The condition has been present for one to four weeks; this is a close-up image; the patient reported no systemic symptoms; the leg is involved; the patient considered this a rash; texture is reported as raised or bumpy; reported lesion symptoms include enlargement, bothersome appearance, burning and itching:
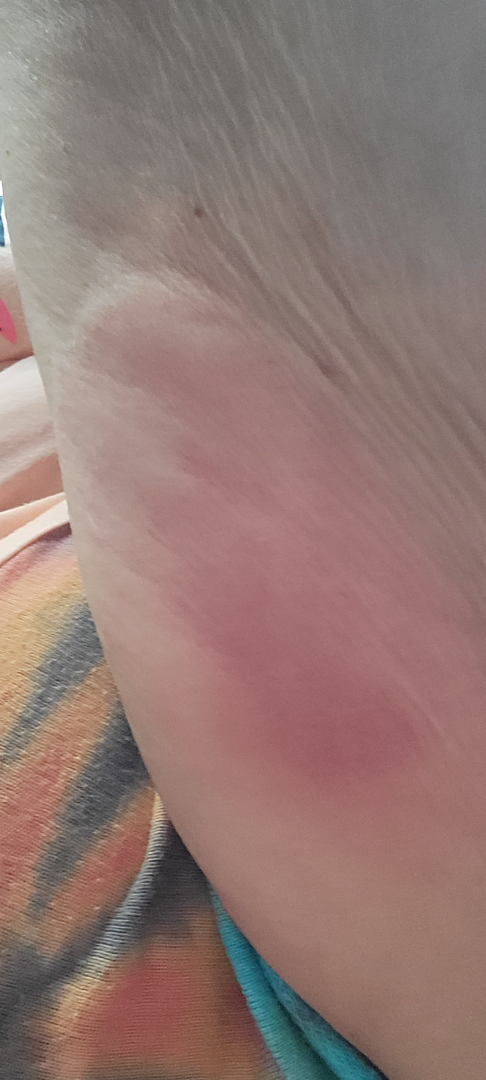Review:
The case was difficult to assess from the available photograph.